The lesion involves the arm, back of the torso and back of the hand; this image was taken at an angle; female contributor, age 30–39 — 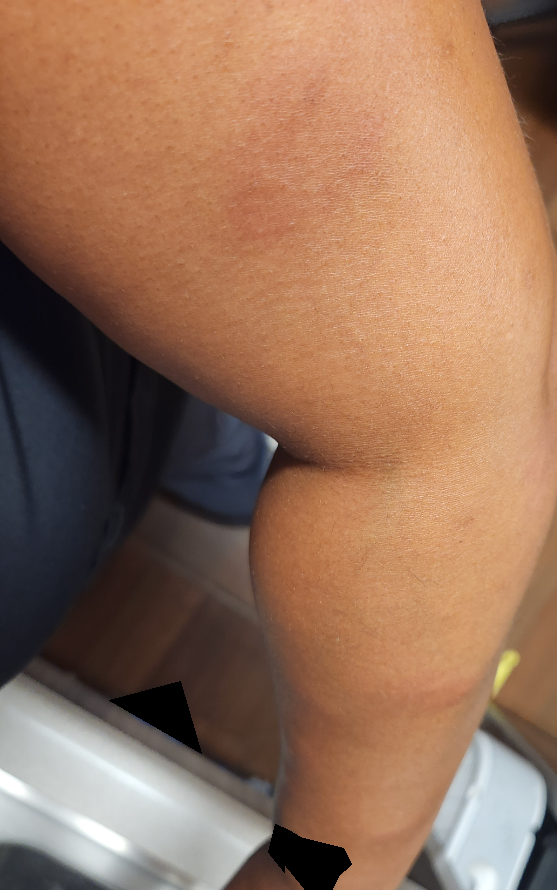  differential:
    leading:
      - Cutaneous lupus
    considered:
      - Urticaria